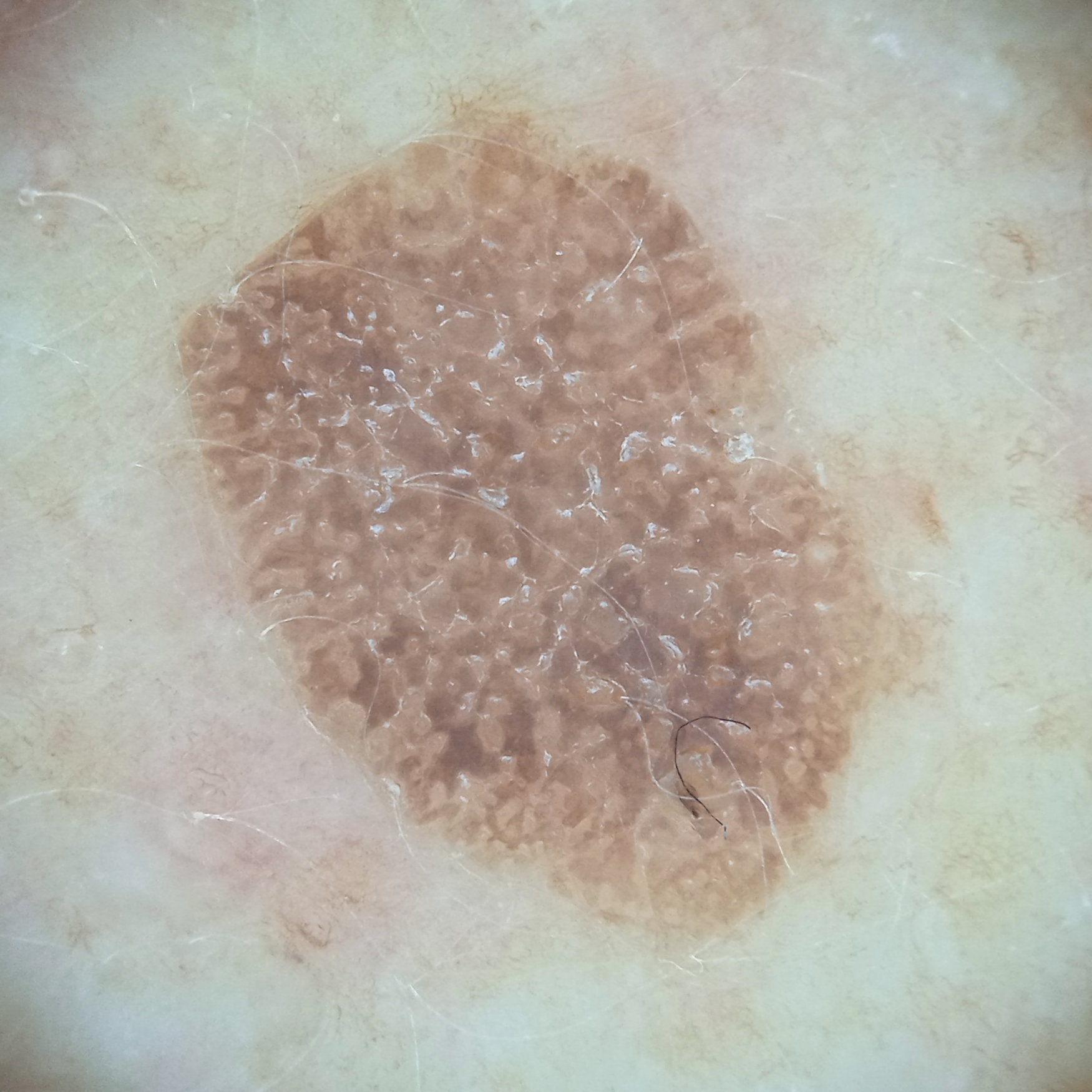A female subject 78 years of age. Imaged for a research study, with no referral diagnosis recorded. A dermatoscopic image of a skin lesion. The lesion is located on the back. Measuring roughly 9.6 mm. The diagnostic impression was a seborrheic keratosis.